A contact-polarized dermoscopy image of a skin lesion · recorded as Fitzpatrick phototype I · a male patient aged approximately 60: 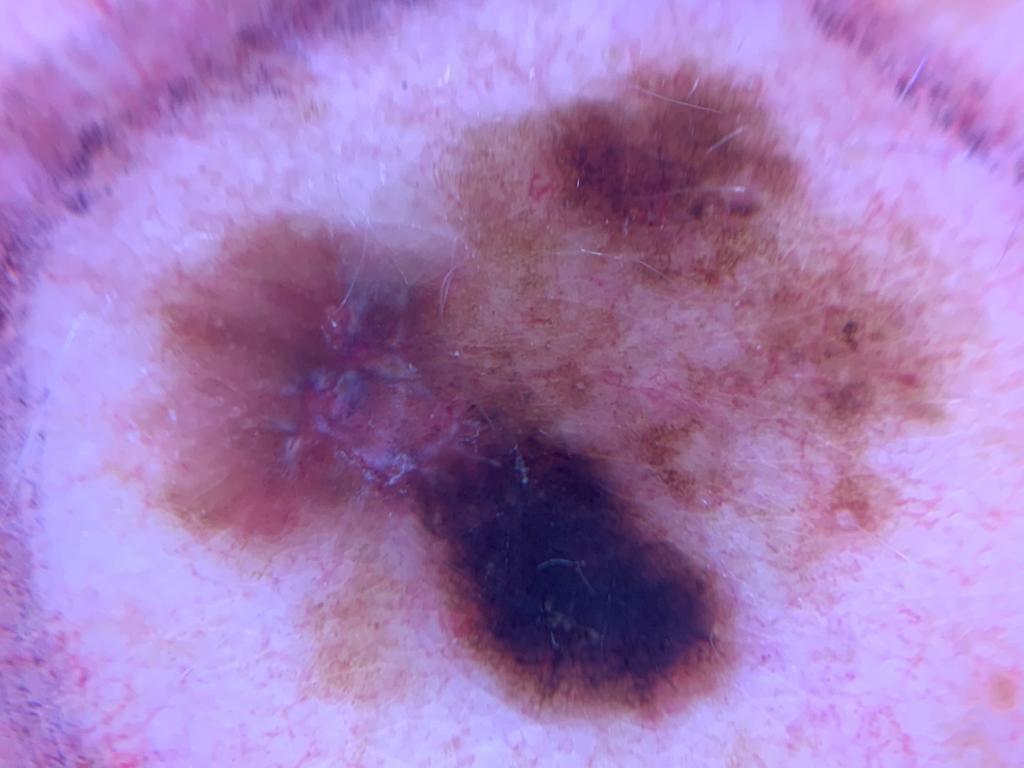The biopsy diagnosis was a malignant lesion — a melanoma.